This is a close-up image — 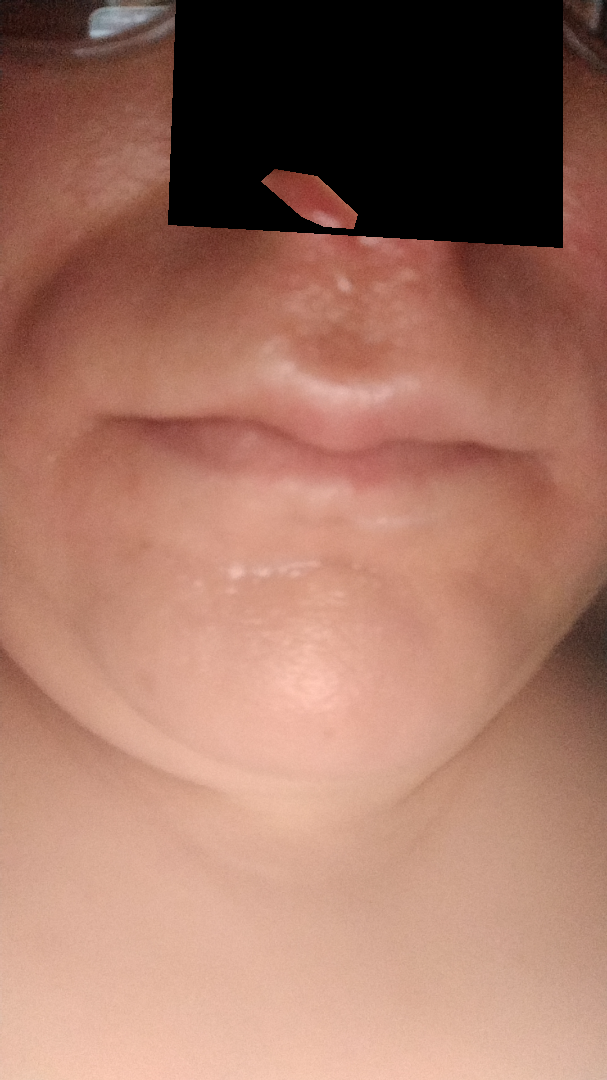The image was not sufficient for the reviewer to characterize the skin condition.
Symptoms reported: burning, pain and itching.
Self-categorized by the patient as a rash.
Reported duration is less than one week.
The contributor reports the lesion is rough or flaky and raised or bumpy.
Skin tone: Fitzpatrick phototype III; lay graders estimated a MST of 3.